A clinical close-up photograph of a skin lesion · a male subject in their 70s:
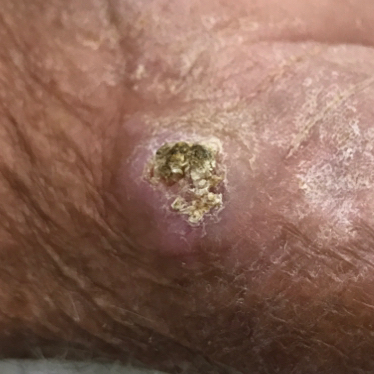Notes:
* region: a hand
* reported symptoms: elevation, itching, bleeding, pain
* diagnostic label: squamous cell carcinoma (biopsy-proven)